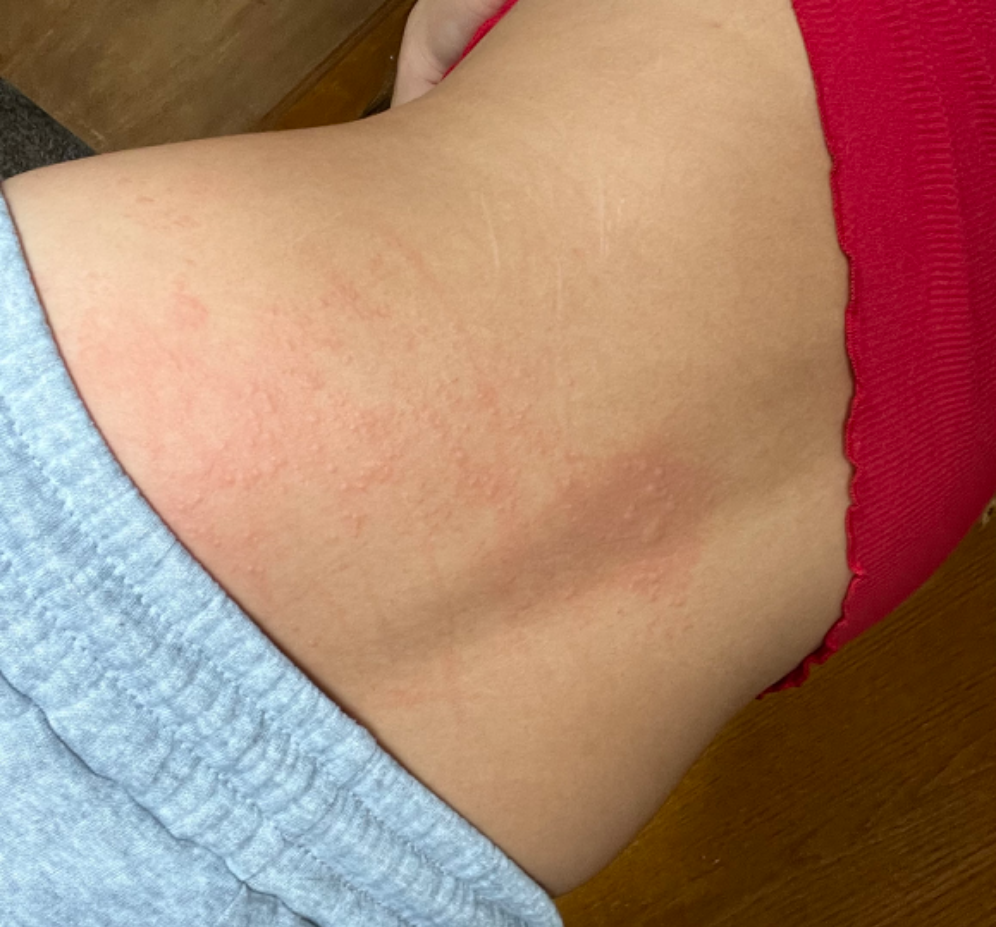body site = back of the torso, image framing = at a distance, clinical impression = the leading consideration is Urticaria; an alternative is Allergic Contact Dermatitis.